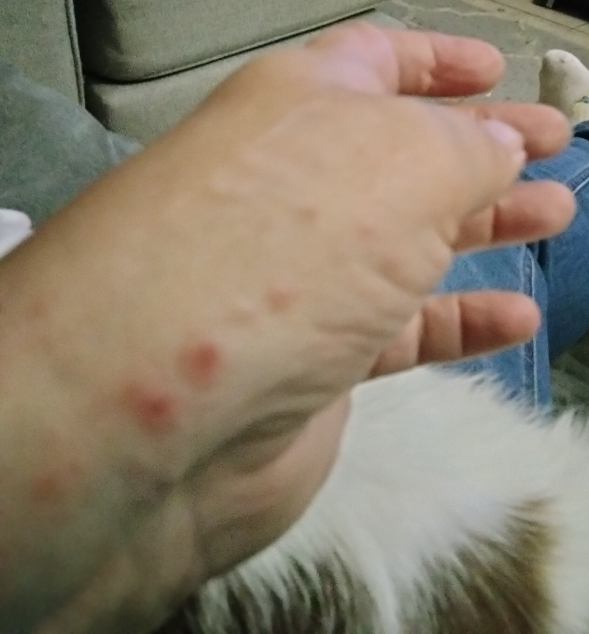Patient information:
Present for less than one week. The lesion involves the back of the hand. Texture is reported as raised or bumpy and fluid-filled. A close-up photograph.
Review:
On photographic review by a dermatologist: Insect Bite (favored); Urticaria (possible); Allergic Contact Dermatitis (possible).